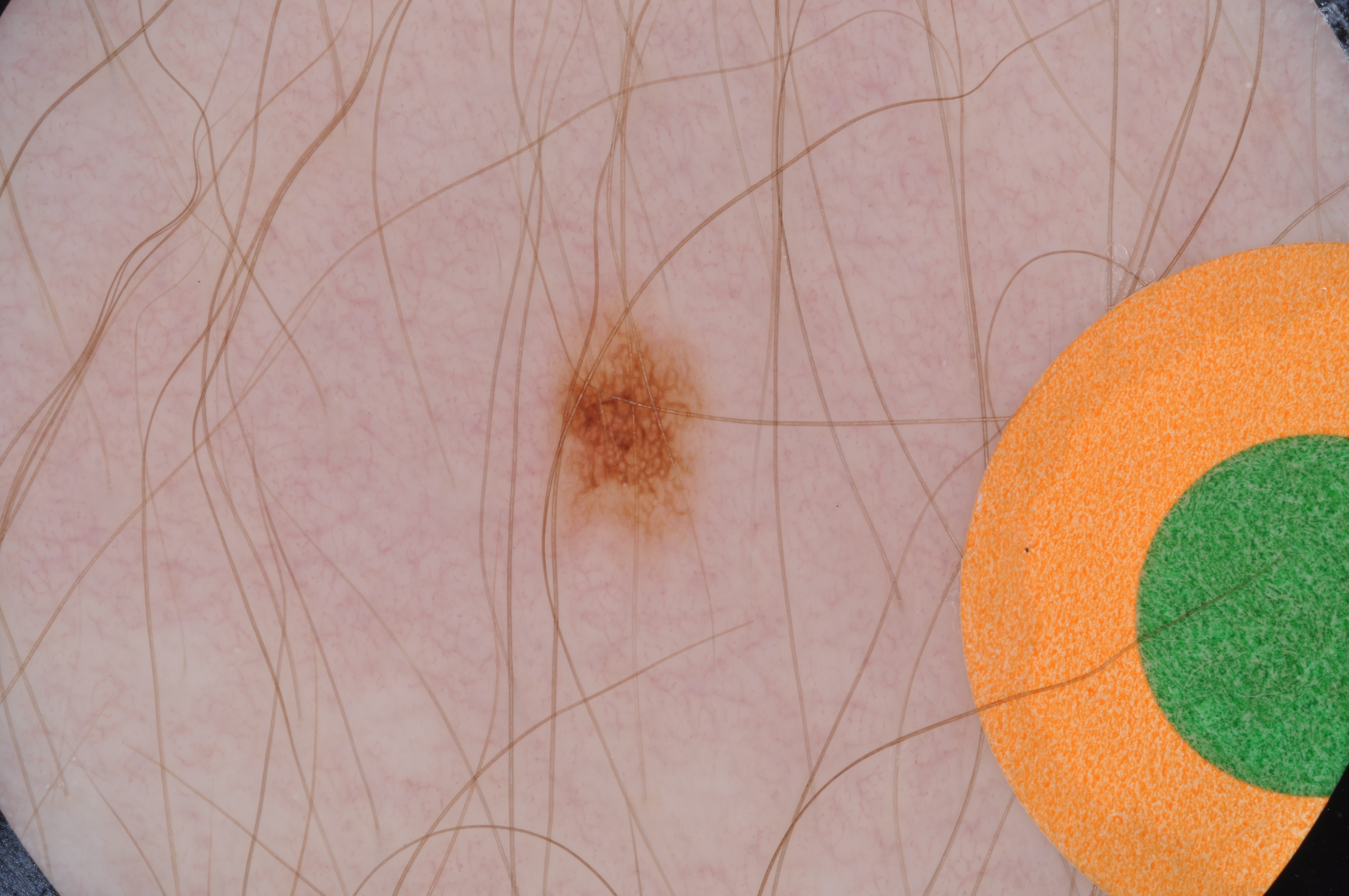A dermoscopic image of a skin lesion.
The dermoscopic pattern shows no globules or streaks.
The lesion is bounded by left=529, top=280, right=720, bottom=567.
Diagnosed as a benign skin lesion.